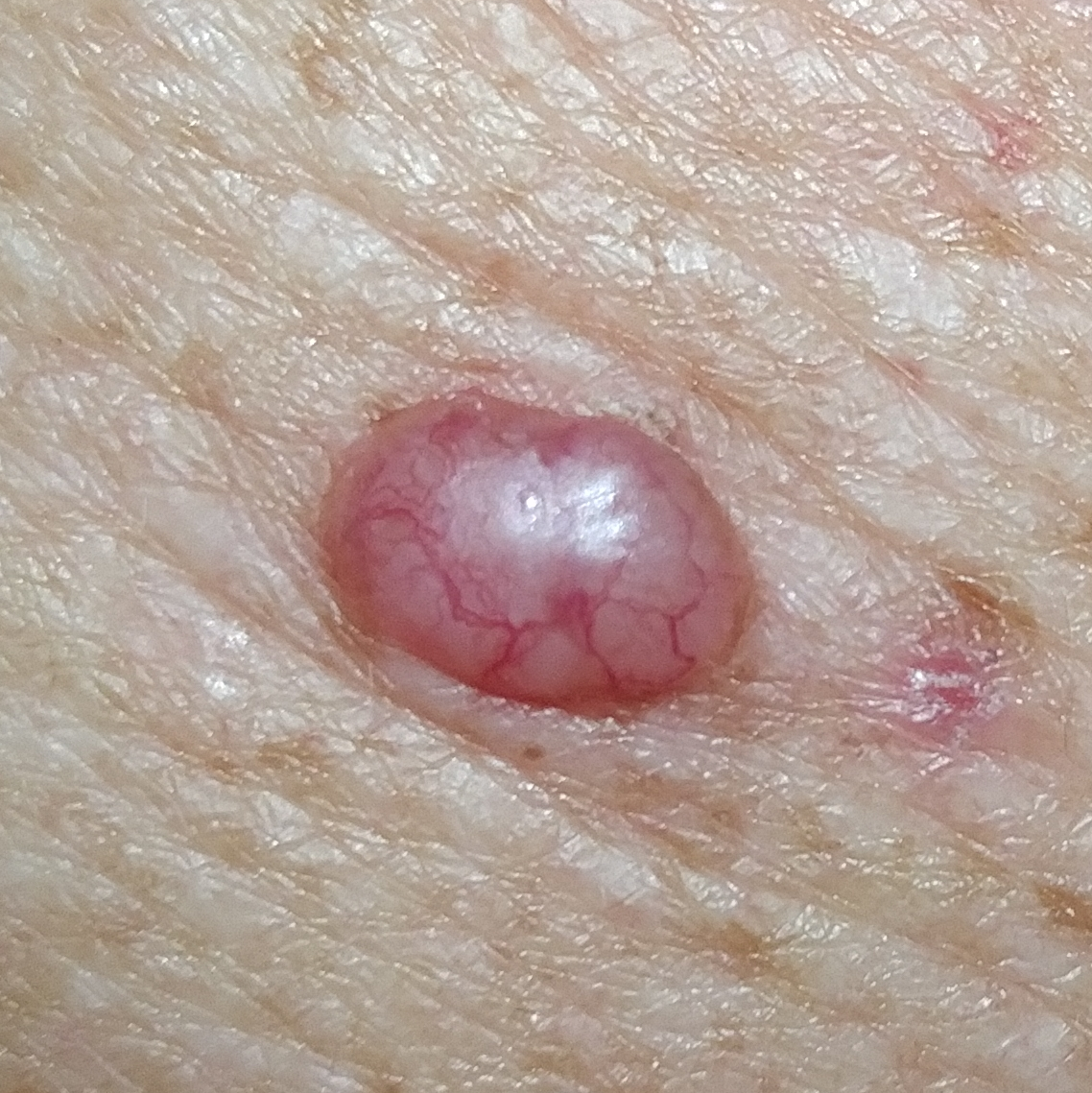A male subject 75 years old.
By history, prior malignancy (patient or family), pesticide exposure, no prior skin cancer (patient or family), and no tobacco use.
The lesion is located on the back.
The biopsy diagnosis was a skin cancer — a basal cell carcinoma.